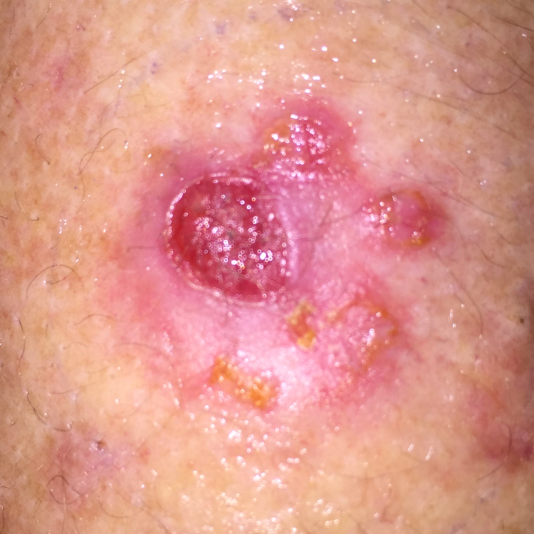Q: How was this image acquired?
A: clinical photo
Q: What are the relevant risk factors?
A: prior malignancy (patient or family), no pesticide exposure, no tobacco use
Q: Tell me about the patient.
A: female, 70 years of age
Q: What are the lesion's dimensions?
A: 11 × 10 mm
Q: What is this lesion?
A: basal cell carcinoma (biopsy-proven)